This image was taken at an angle · located on the head or neck and arm: 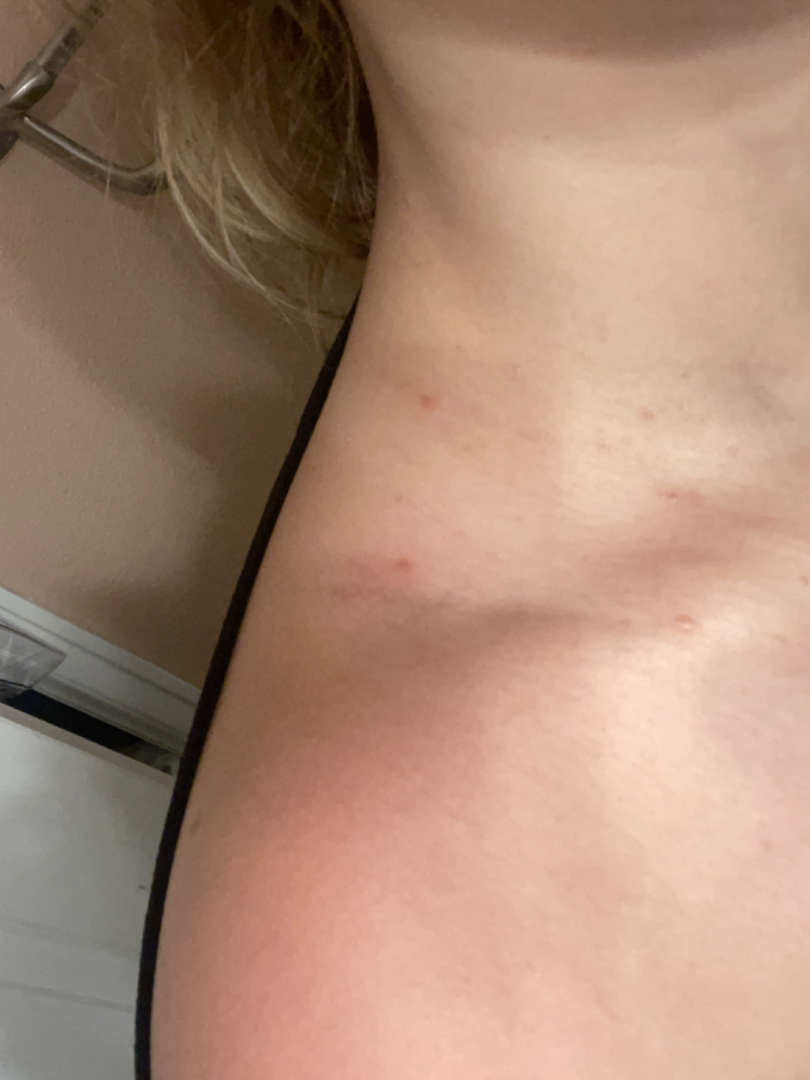  assessment: unable to determine